Collected as part of a research study, without a referral diagnosis. A clinical close-up of a skin lesion. A male patient 76 years of age. The patient says their skin reddens with sun exposure. On a questionnaire the patient reported a personal history of cancer, a personal history of skin cancer, no sunbed use, and no family history of skin cancer — 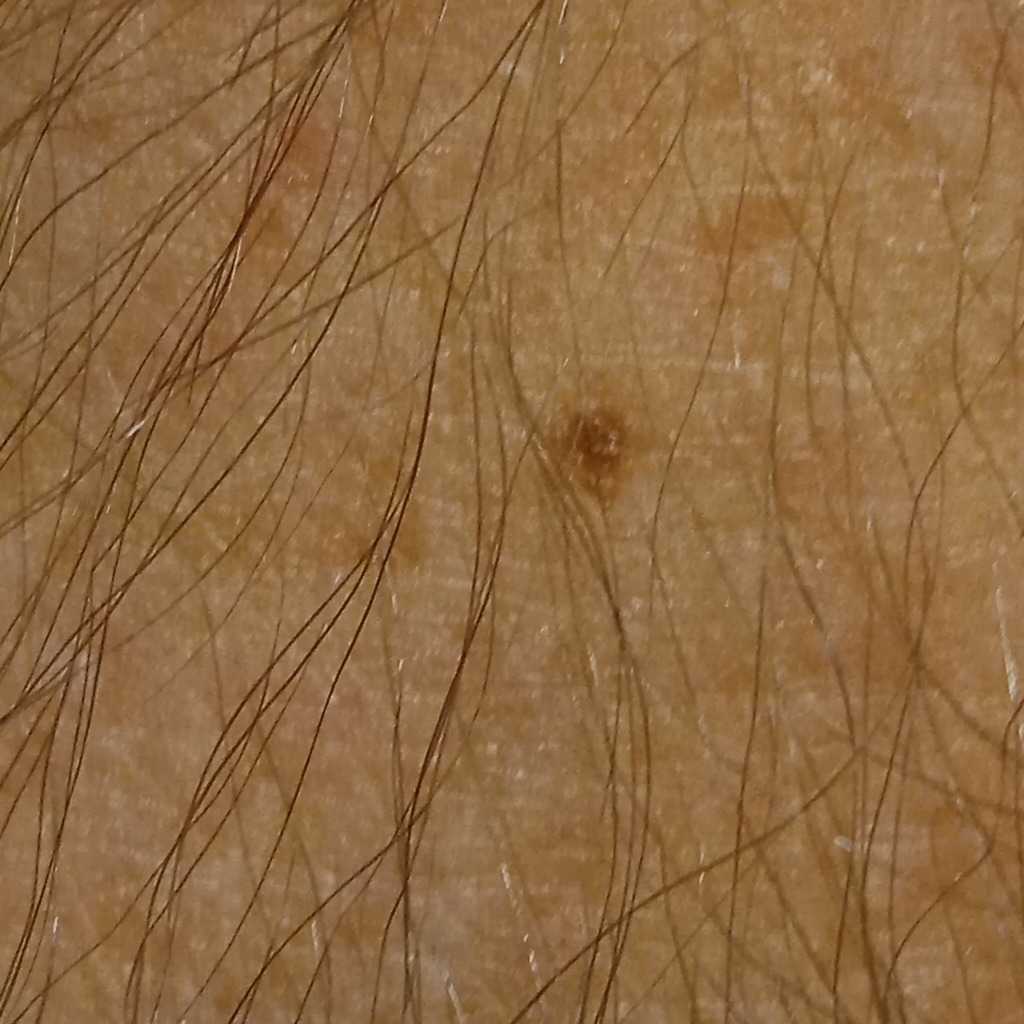{
  "lesion_location": "an arm",
  "lesion_size": {
    "diameter_mm": 8.2
  },
  "diagnosis": {
    "name": "melanocytic nevus",
    "malignancy": "benign"
  }
}